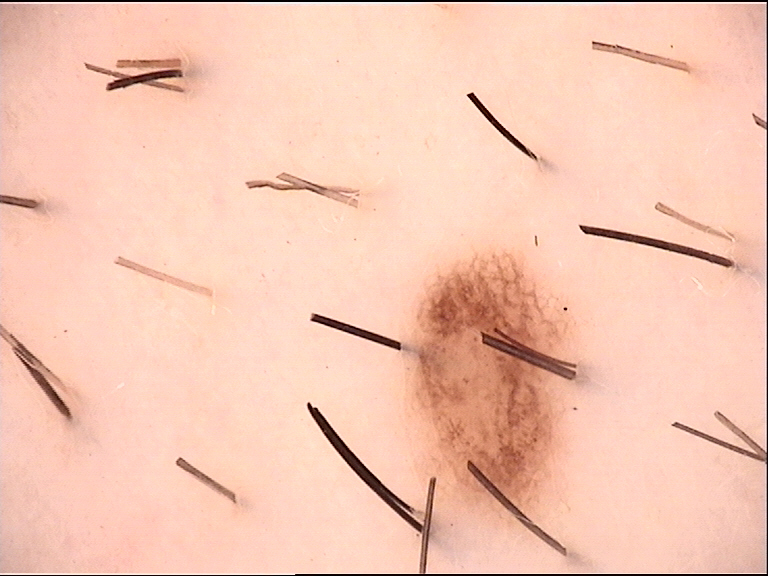| key | value |
|---|---|
| image type | dermoscopy |
| diagnosis | dysplastic junctional nevus (expert consensus) |